The patient is 40–49, female · the condition has been present for one to four weeks · located on the arm · the photograph is a close-up of the affected area: 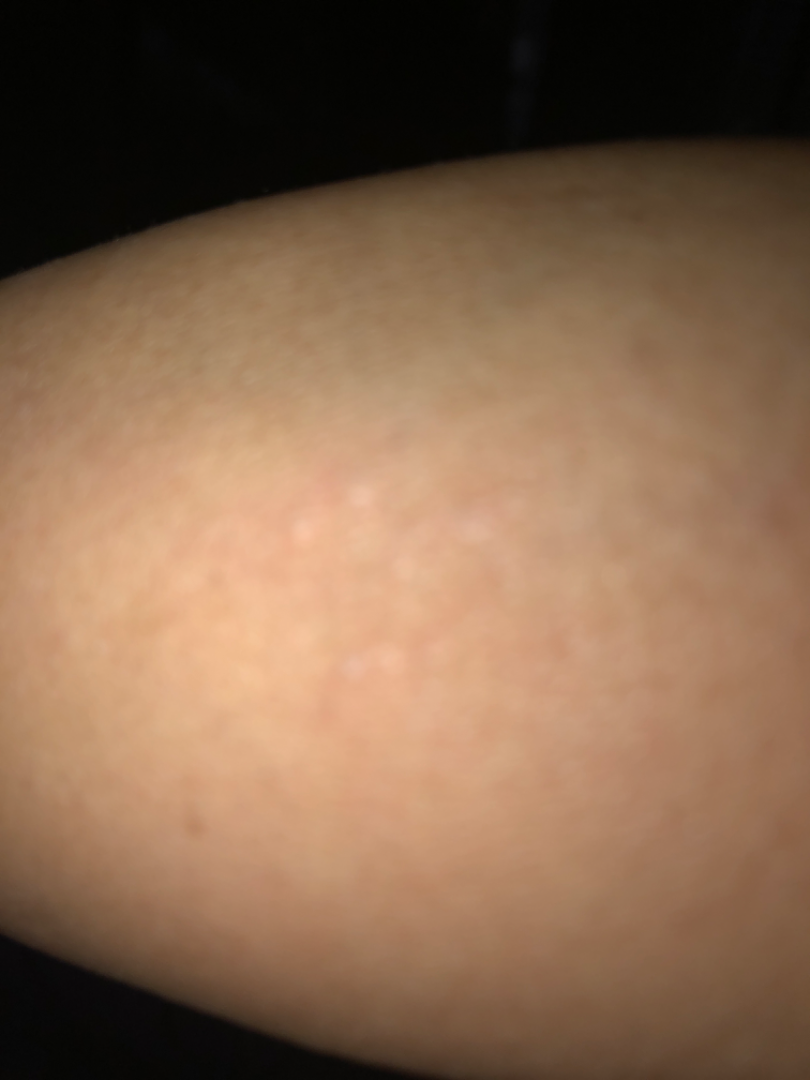Notes:
– assessment · indeterminate from the photograph